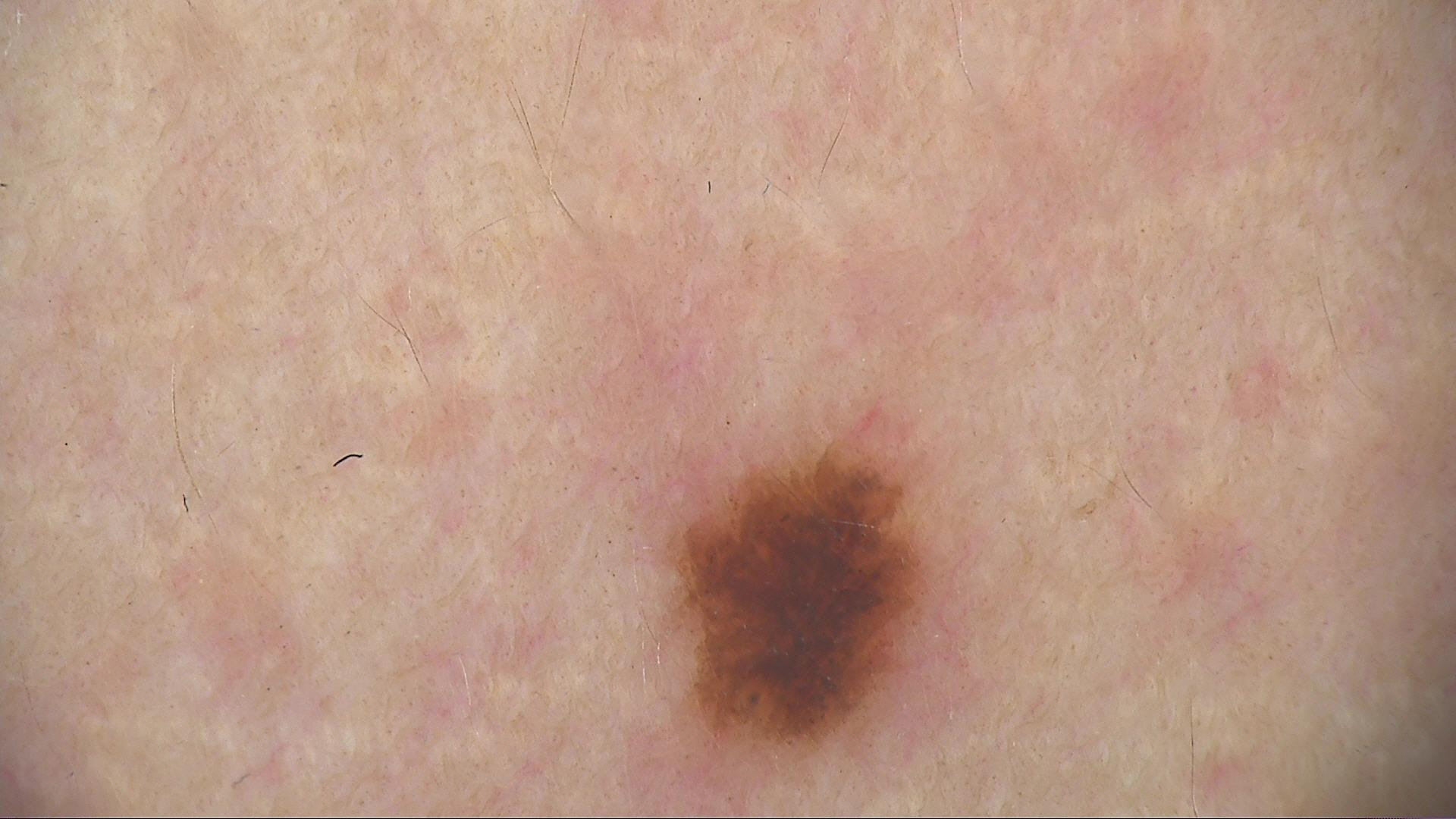A dermoscopic image of a skin lesion. Diagnosed as a dysplastic junctional nevus.